This is a close-up image: 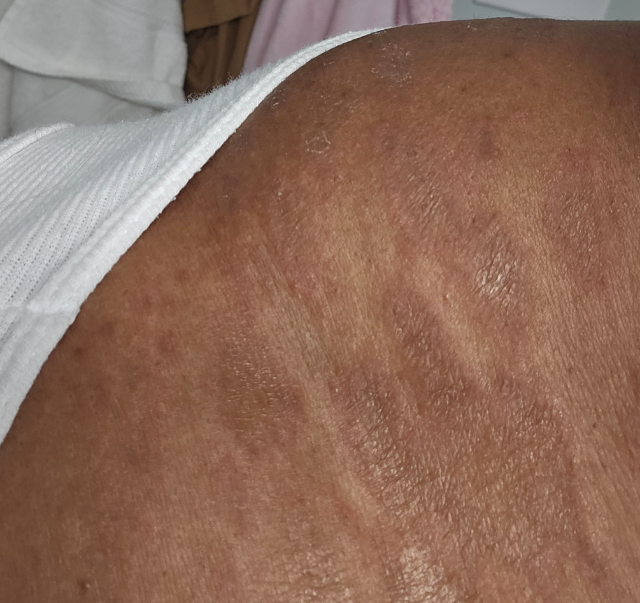| field | value |
|---|---|
| clinical impression | most likely Pityriasis rosea |